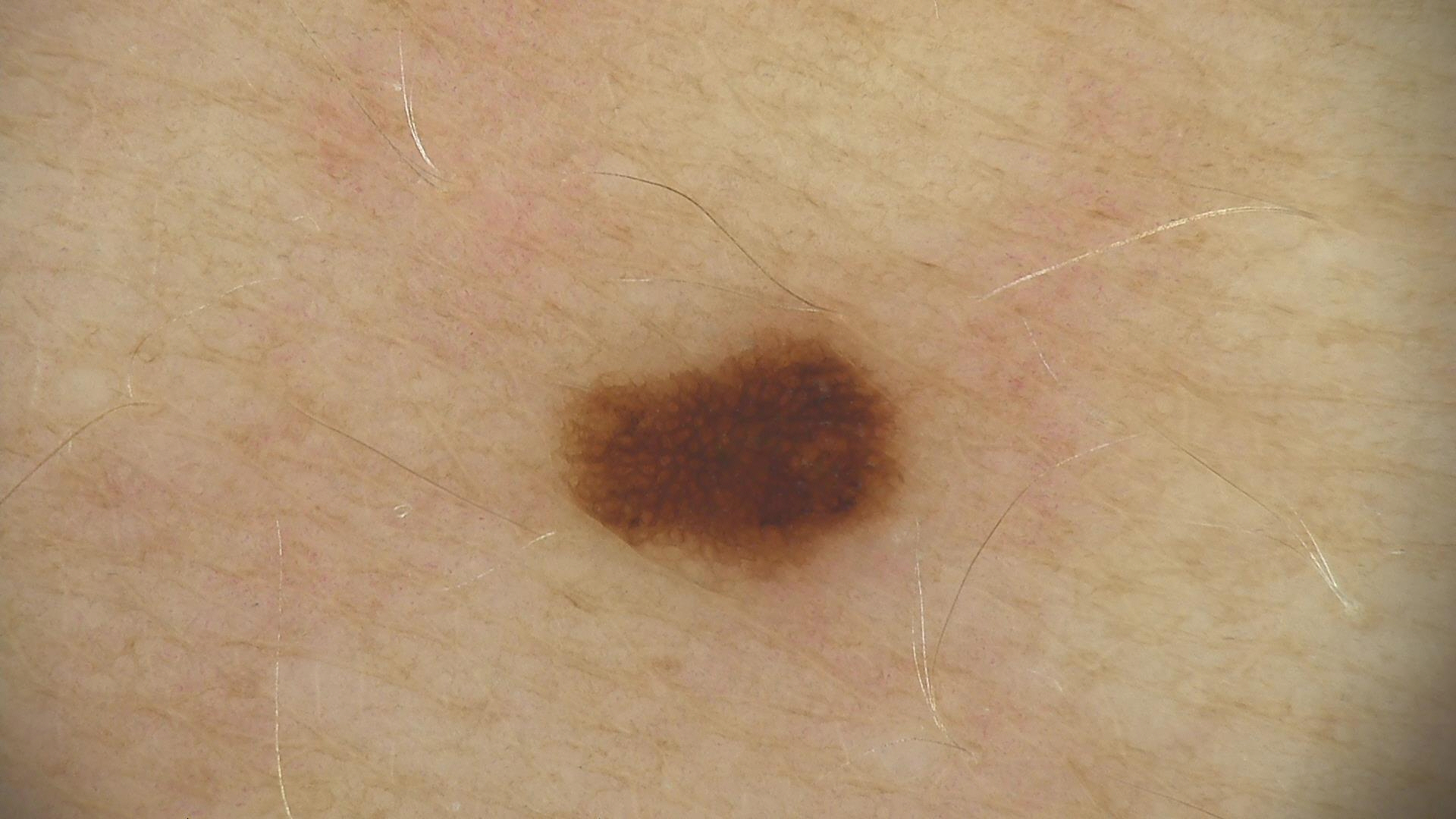<lesion>
  <diagnosis>
    <name>dysplastic junctional nevus</name>
    <code>jd</code>
    <malignancy>benign</malignancy>
    <super_class>melanocytic</super_class>
    <confirmation>expert consensus</confirmation>
  </diagnosis>
</lesion>